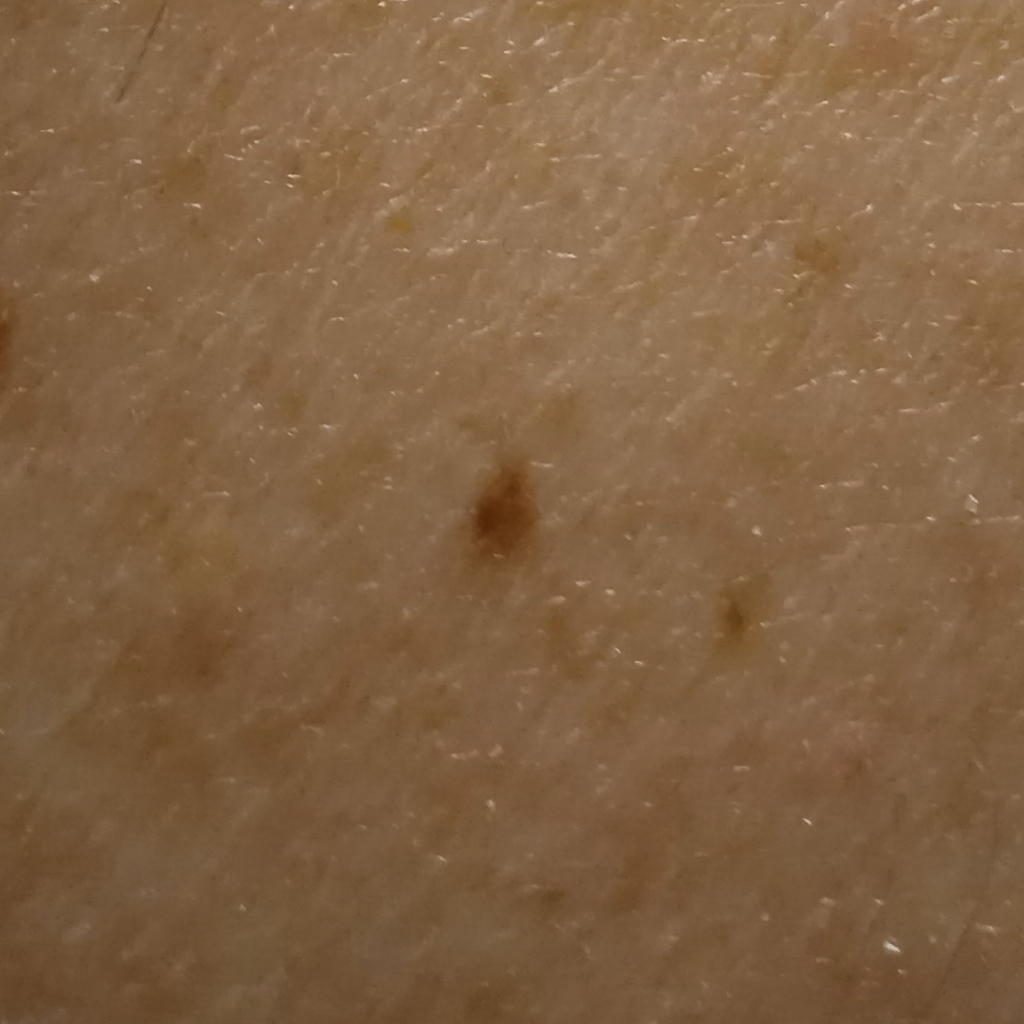– relevant history · a personal history of skin cancer, a family history of skin cancer, a personal history of cancer
– sun reaction · skin tans without first burning
– image type · clinical photograph
– referral · clinical suspicion of melanocytic nevus
– patient · male, 58 years old
– anatomic site · the back
– diameter · 3.2 mm
– assessment · melanocytic nevus (dermatologist consensus)